The patient described the issue as a rash, the lesion is described as flat, the patient indicates the condition has been present for one to four weeks, Fitzpatrick II, a close-up photograph, located on the leg — 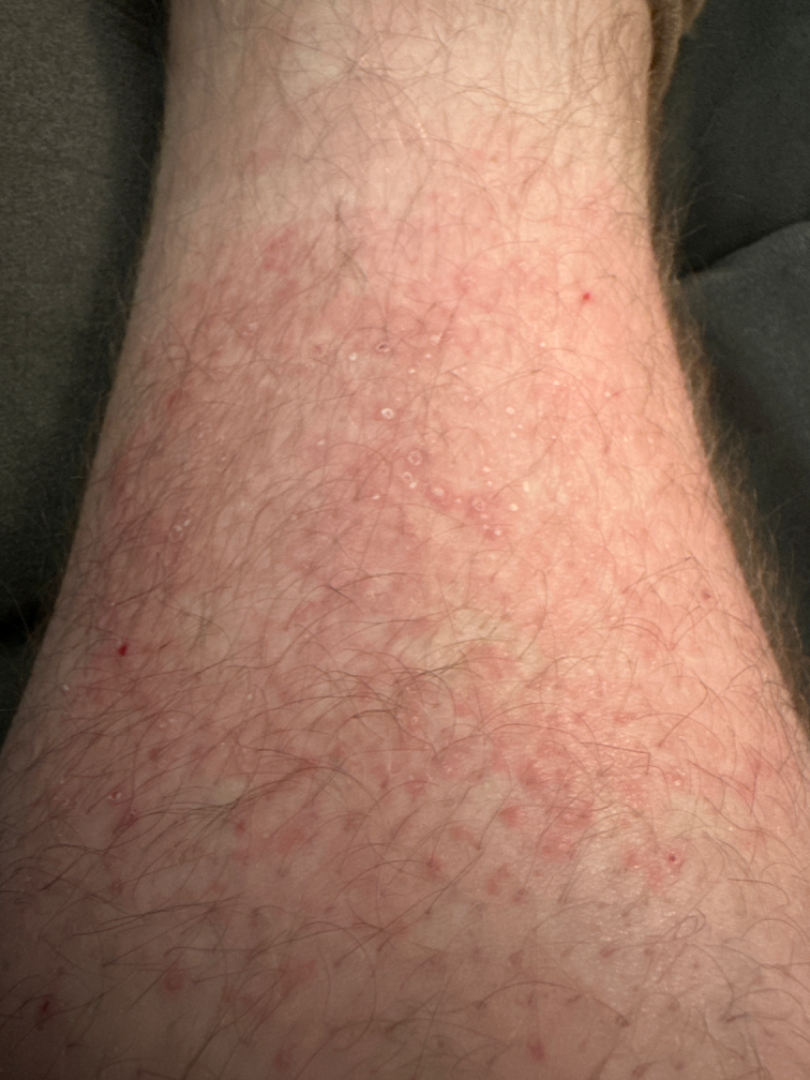Keratosis pilaris and Eczema were each considered, in no particular order; a more distant consideration is Inflammatory dermatosis.